The patient is a female approximately 35 years of age, this is a dermoscopic photograph of a skin lesion:
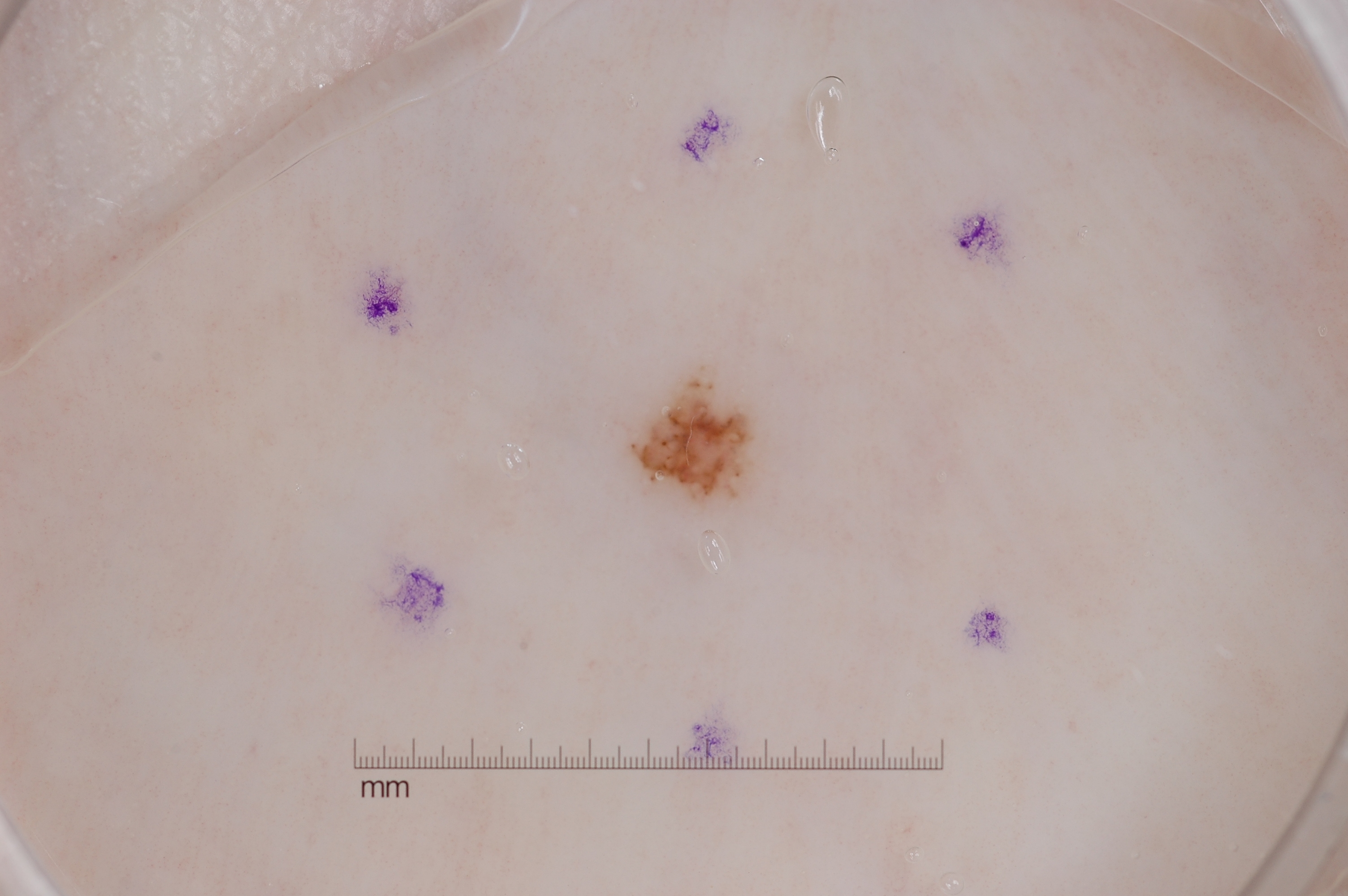dermoscopic features assessed but absent = streaks, pigment network, negative network, and milia-like cysts
lesion location = x1=624, y1=365, x2=758, y2=510
lesion extent = ~1% of the field
diagnostic label = a melanocytic nevus, a benign skin lesion